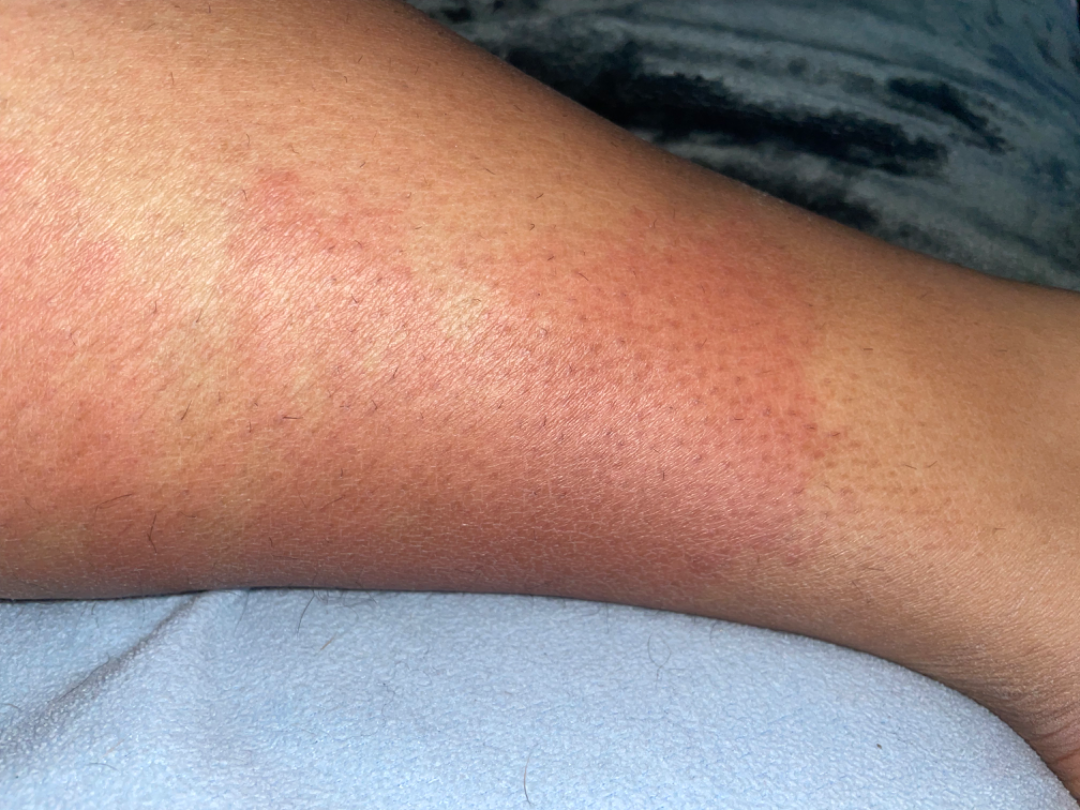Findings:
On photographic review by a dermatologist, Hypersensitivity (favored); Urticaria (possible); Irritant Contact Dermatitis (less likely).